A dermoscopic close-up of a skin lesion · the chart records a prior melanoma but no melanoma in first-degree relatives · recorded as Fitzpatrick II — 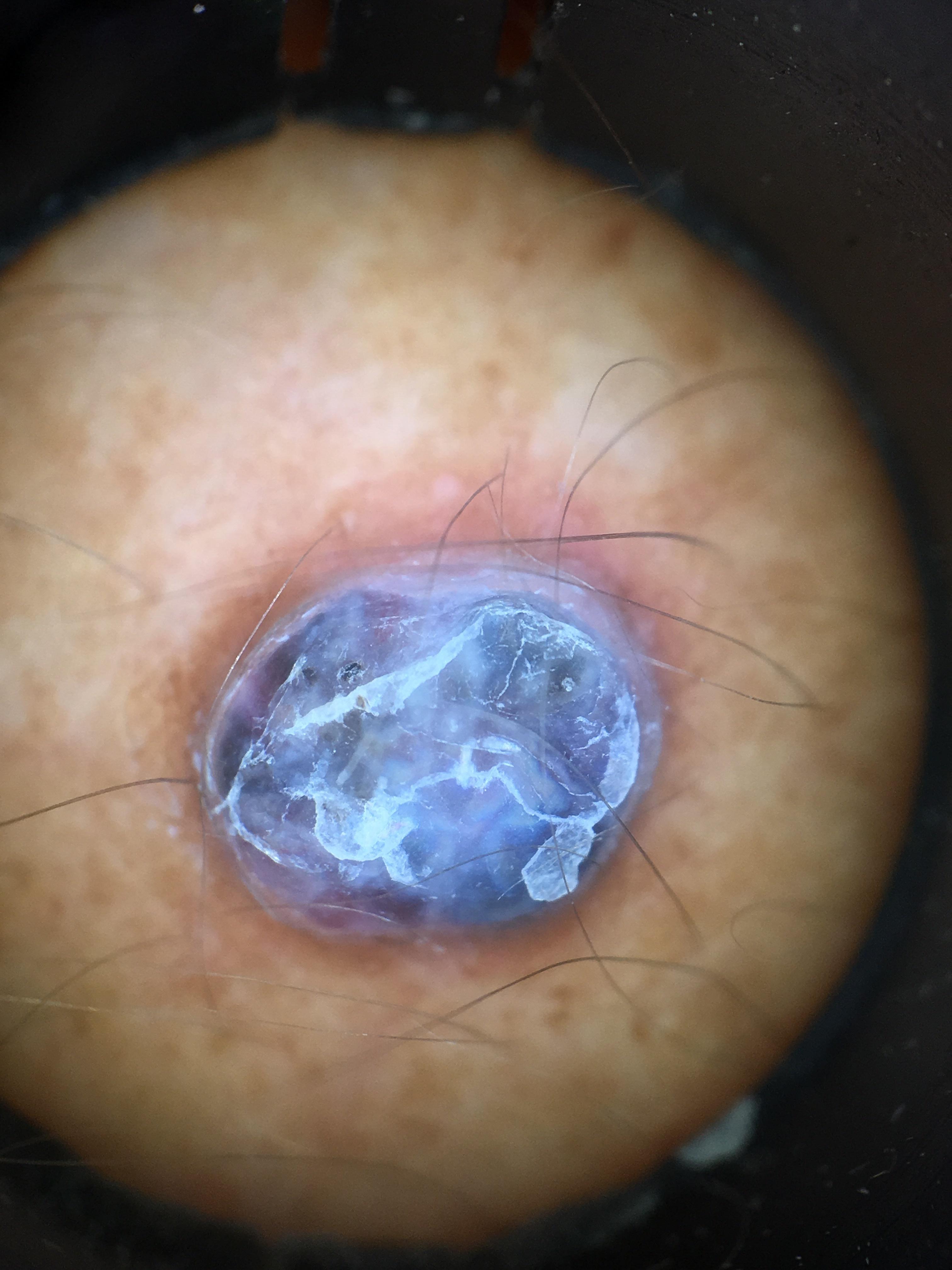Q: Where on the body is the lesion?
A: an upper extremity
Q: What is this lesion?
A: Melanoma (biopsy-proven)